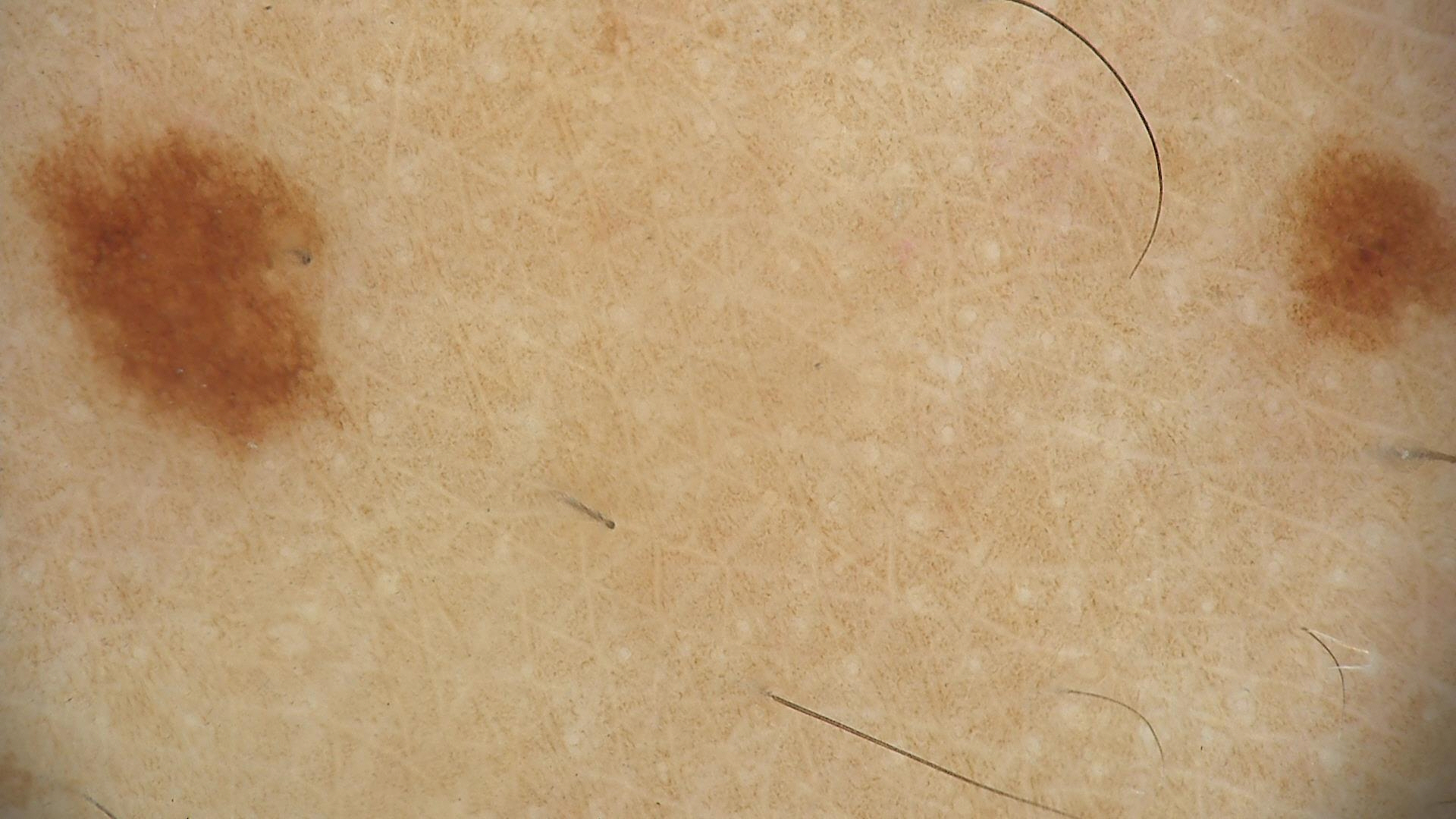imaging = dermatoscopy
label = dysplastic junctional nevus (expert consensus)